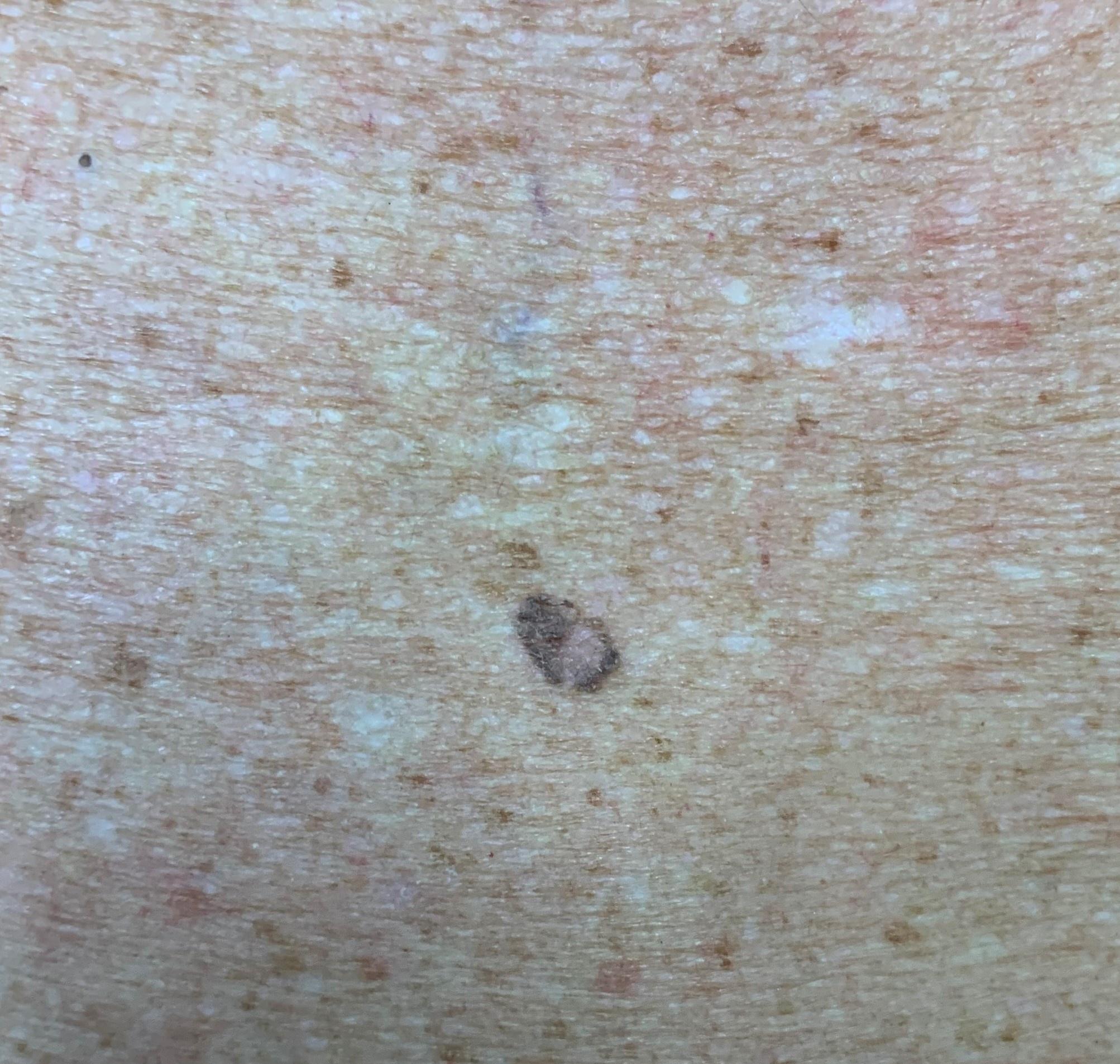Image and clinical context:
A male patient aged approximately 65.
Conclusion:
Histopathology confirmed a seborrheic keratosis.